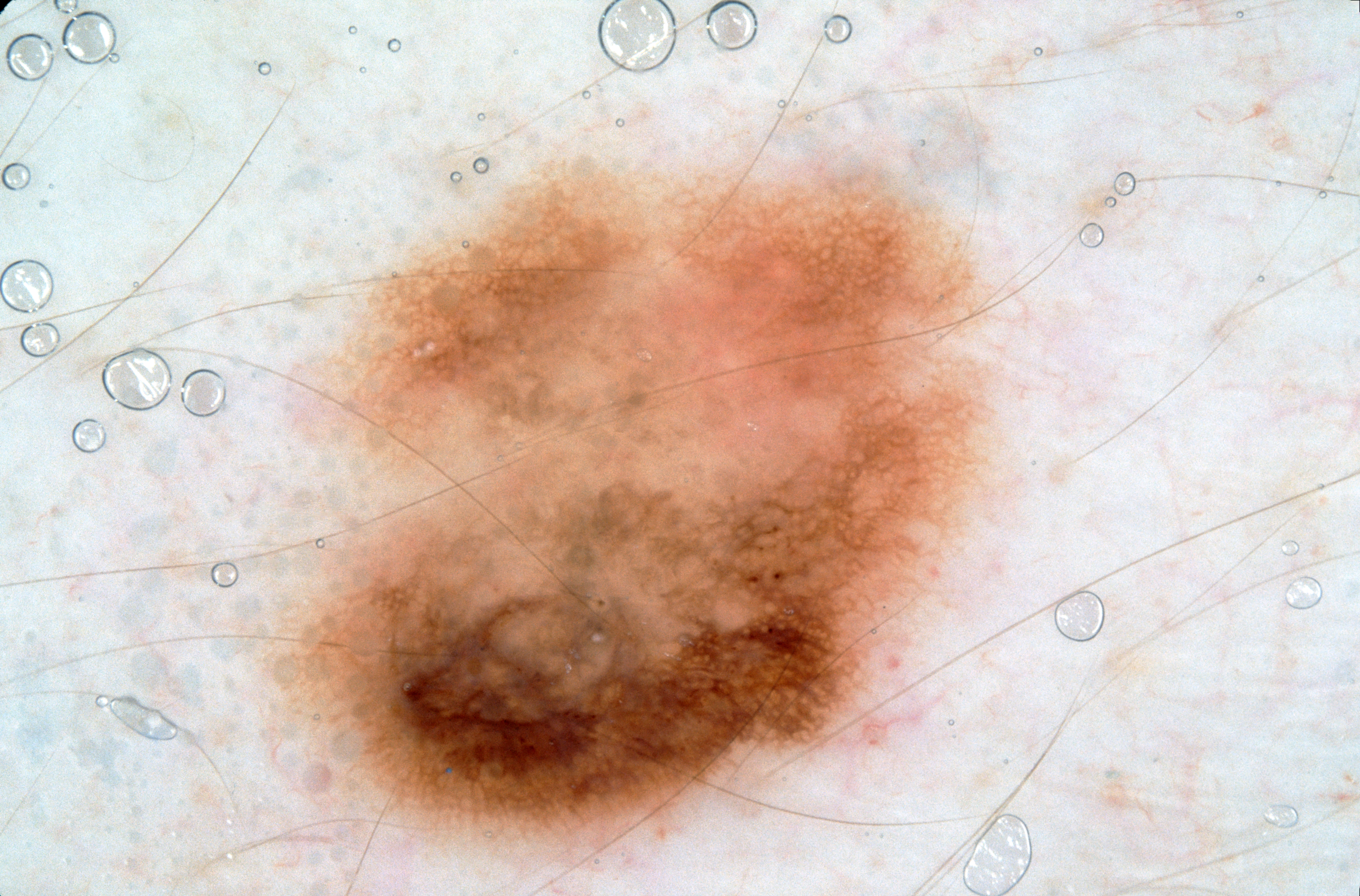| key | value |
|---|---|
| image type | dermoscopy of a skin lesion |
| features | pigment network |
| bounding box | <box>262, 156, 1006, 867</box> |
| diagnosis | a melanocytic nevus |